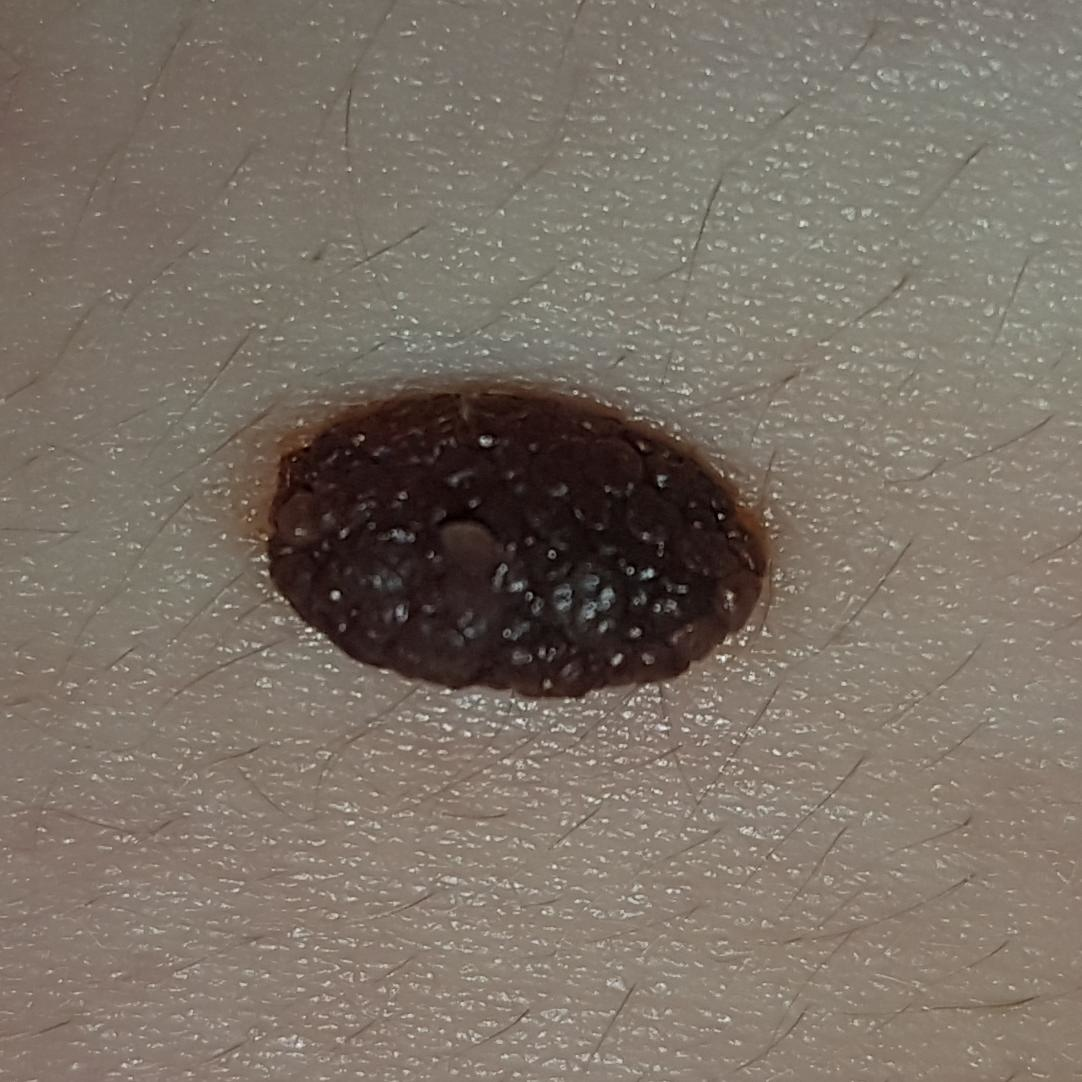{"patient": {"age": 36}, "image": "clinical photograph", "lesion_location": "the chest", "diagnosis": {"name": "nevus", "code": "NEV", "malignancy": "benign", "confirmation": "clinical consensus"}}